Dermoscopy of a skin lesion:
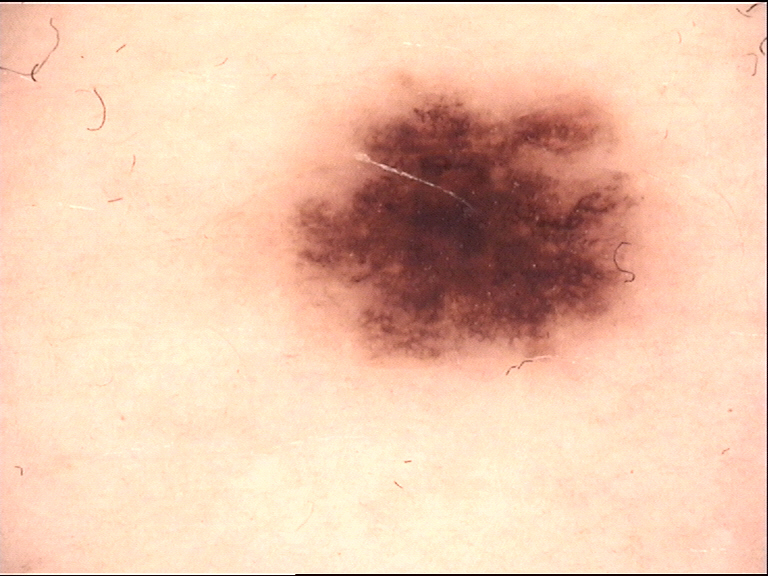Labeled as a dysplastic junctional nevus.